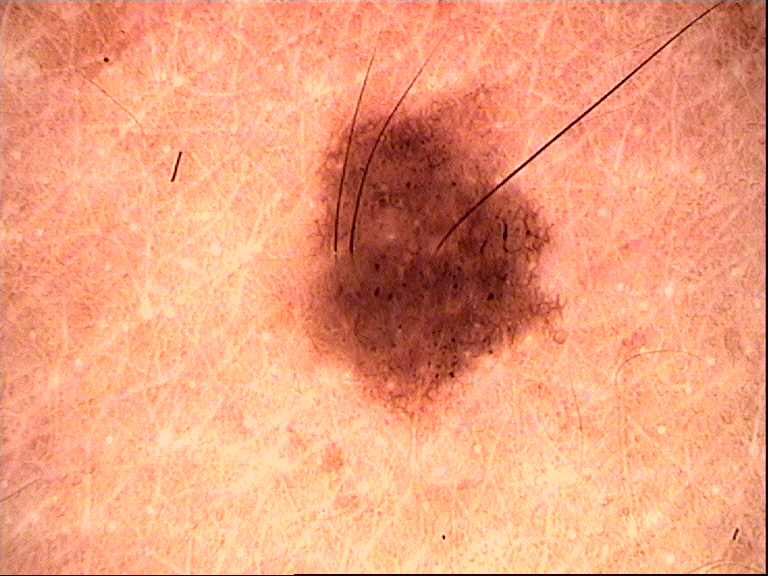Summary:
A dermoscopic close-up of a skin lesion.
Impression:
The diagnostic label was a benign lesion — a dysplastic compound nevus.